The lesion involves the palm · a close-up photograph — 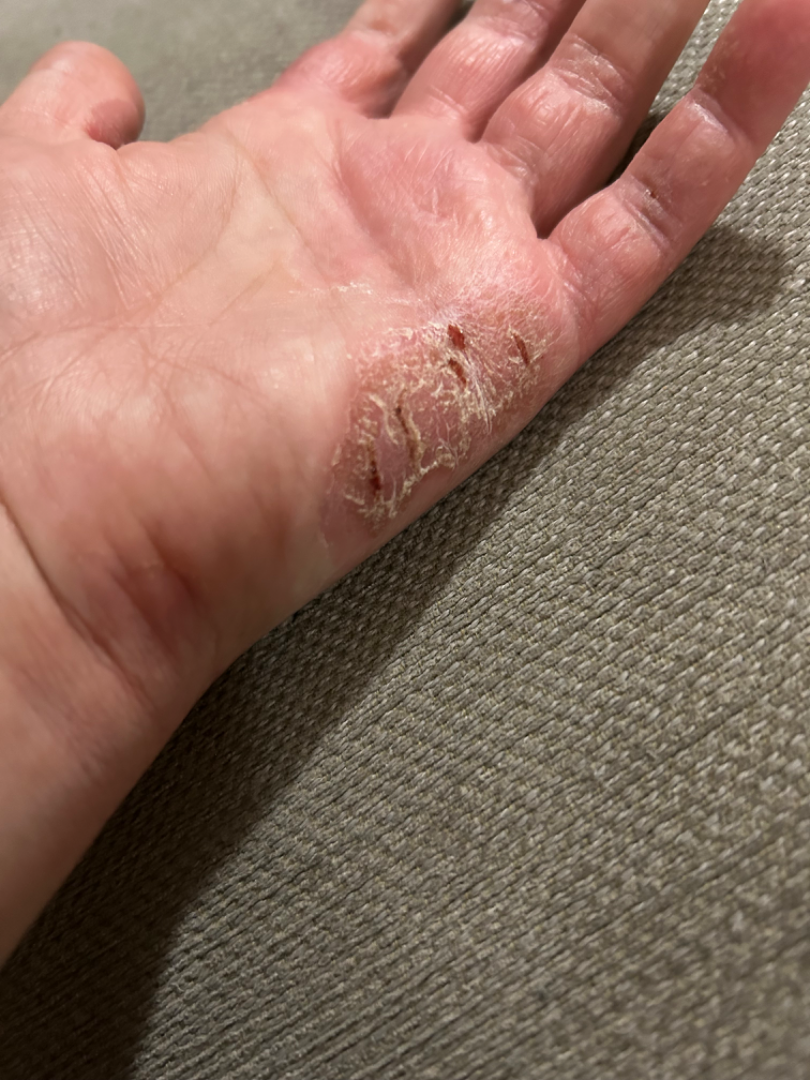On photographic review: the favored diagnosis is Irritant Contact Dermatitis; also consider Psoriasis; with consideration of Allergic Contact Dermatitis.